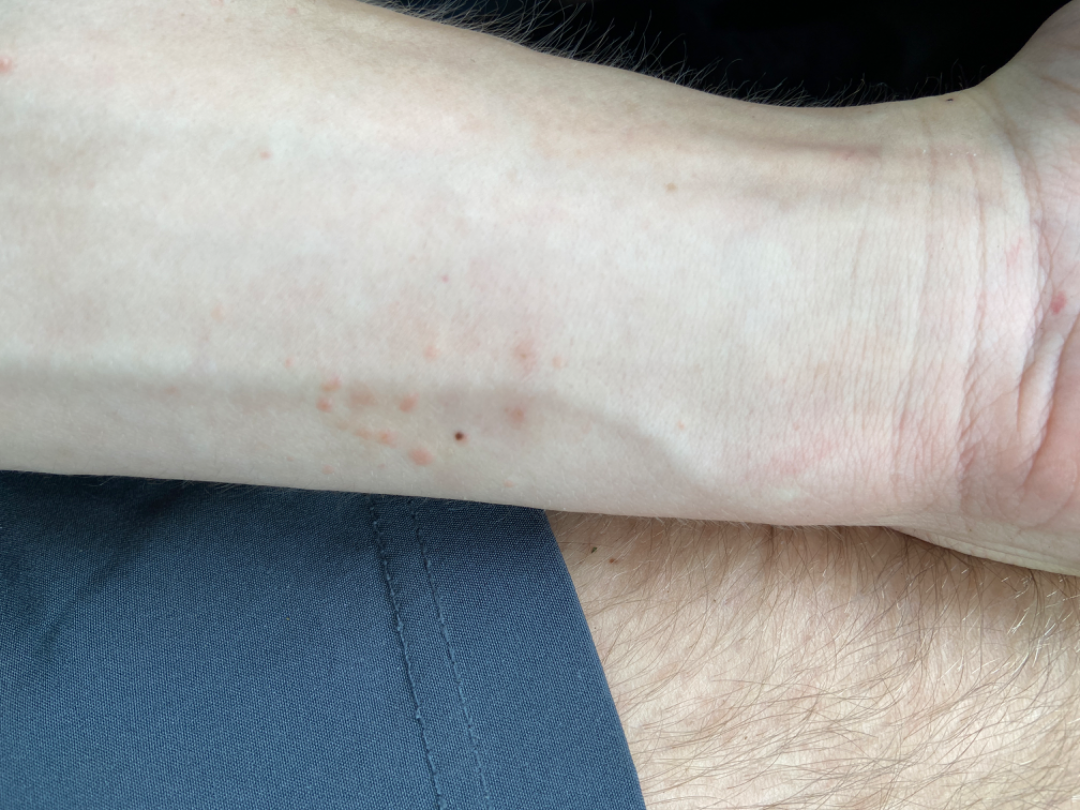{
  "duration": "one to four weeks",
  "texture": "raised or bumpy",
  "body_site": [
    "arm",
    "palm",
    "back of the hand"
  ],
  "shot_type": "close-up",
  "differential": {
    "tied_lead": [
      "Granuloma annulare",
      "Insect Bite",
      "Allergic Contact Dermatitis"
    ]
  }
}